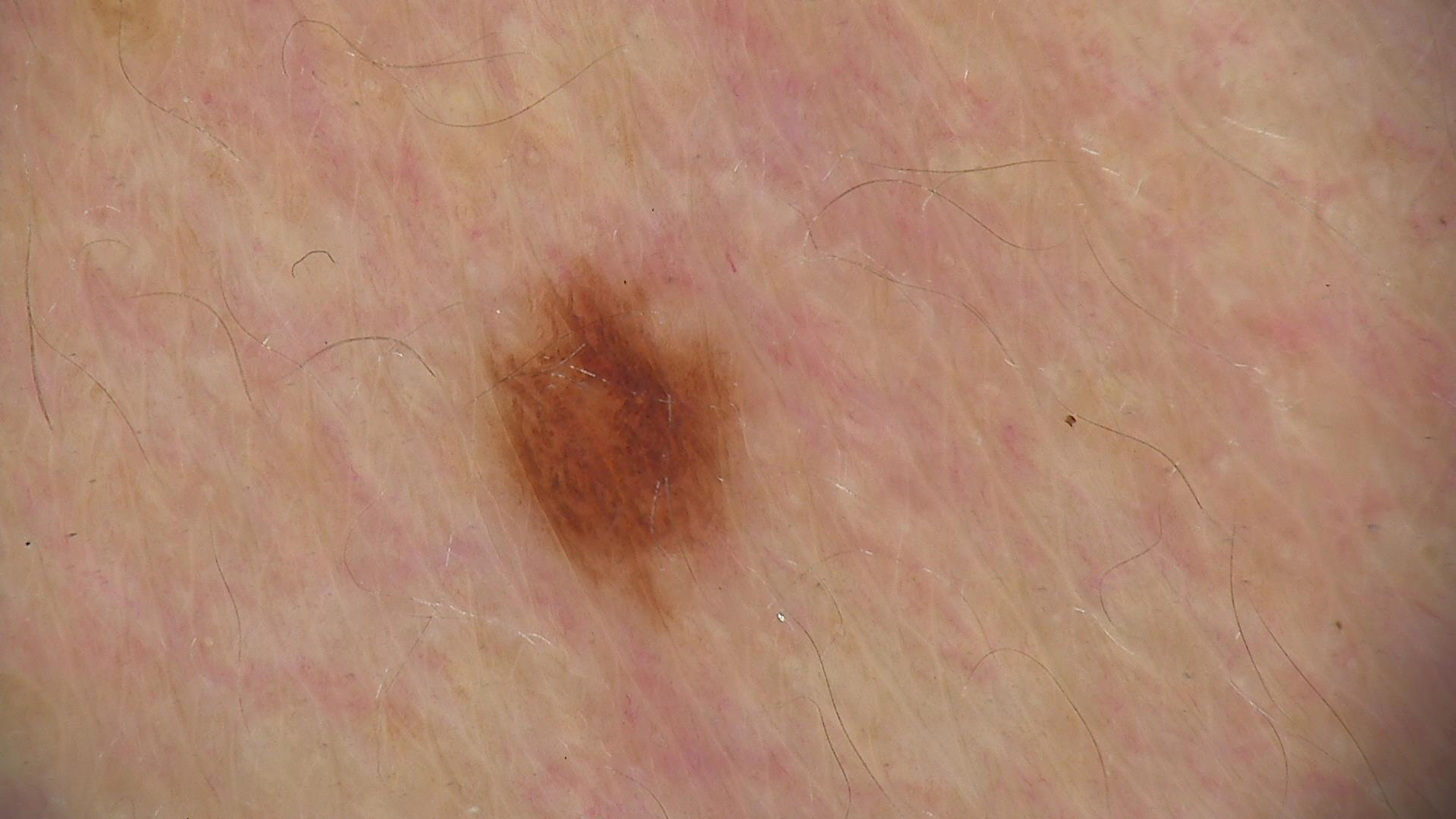Q: What is the diagnosis?
A: dysplastic junctional nevus (expert consensus)